The photograph was taken at an angle · the affected area is the back of the torso, head or neck, arm, leg and back of the hand · the contributor is 40–49, female: 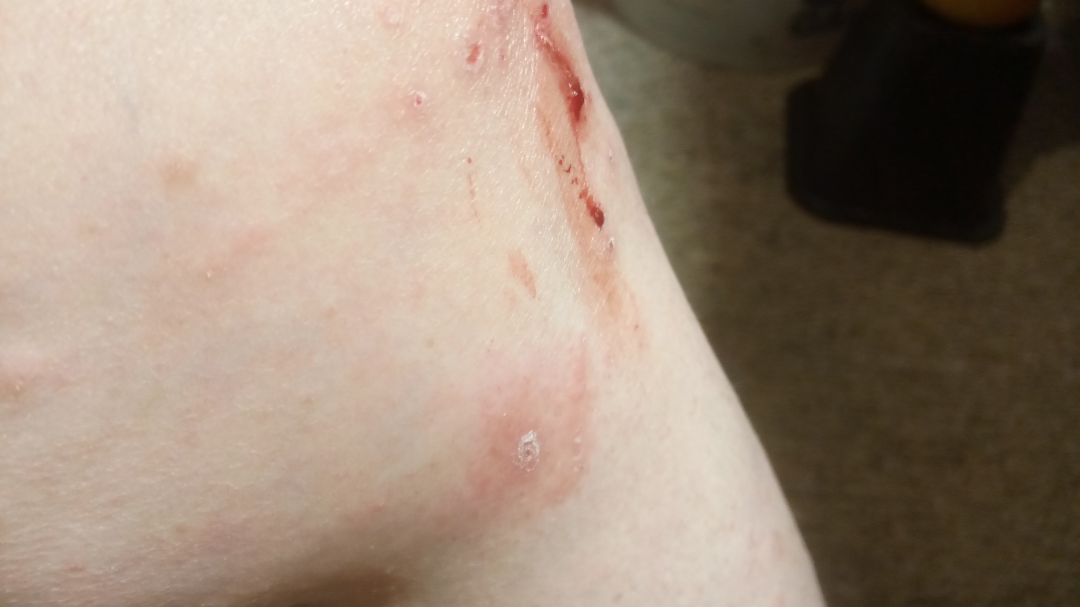clinical impression = three dermatologists each reviewed the case: in keeping with Allergic Contact Dermatitis.